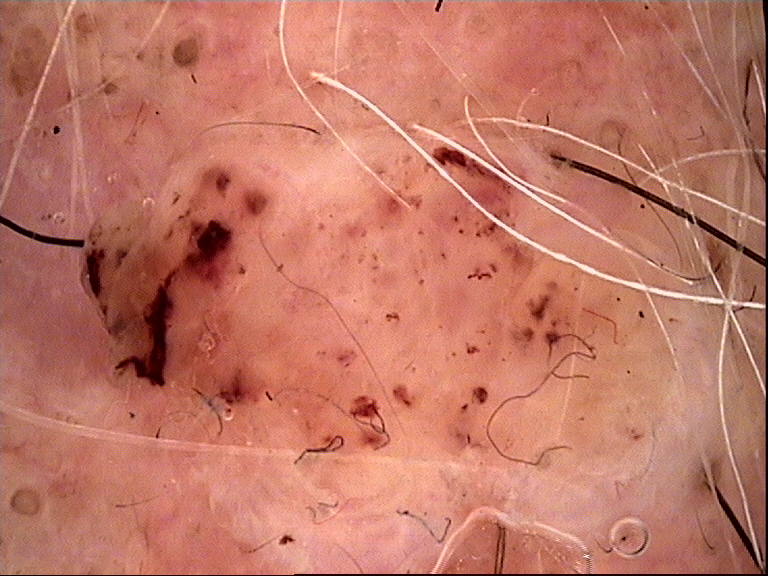image = dermoscopy | diagnostic label = dermal nevus (expert consensus).